Acquired for a research image collection, with no referral diagnosis. A male subject aged 73. The patient describes having numerous moles. A dermatoscopic image of a skin lesion — 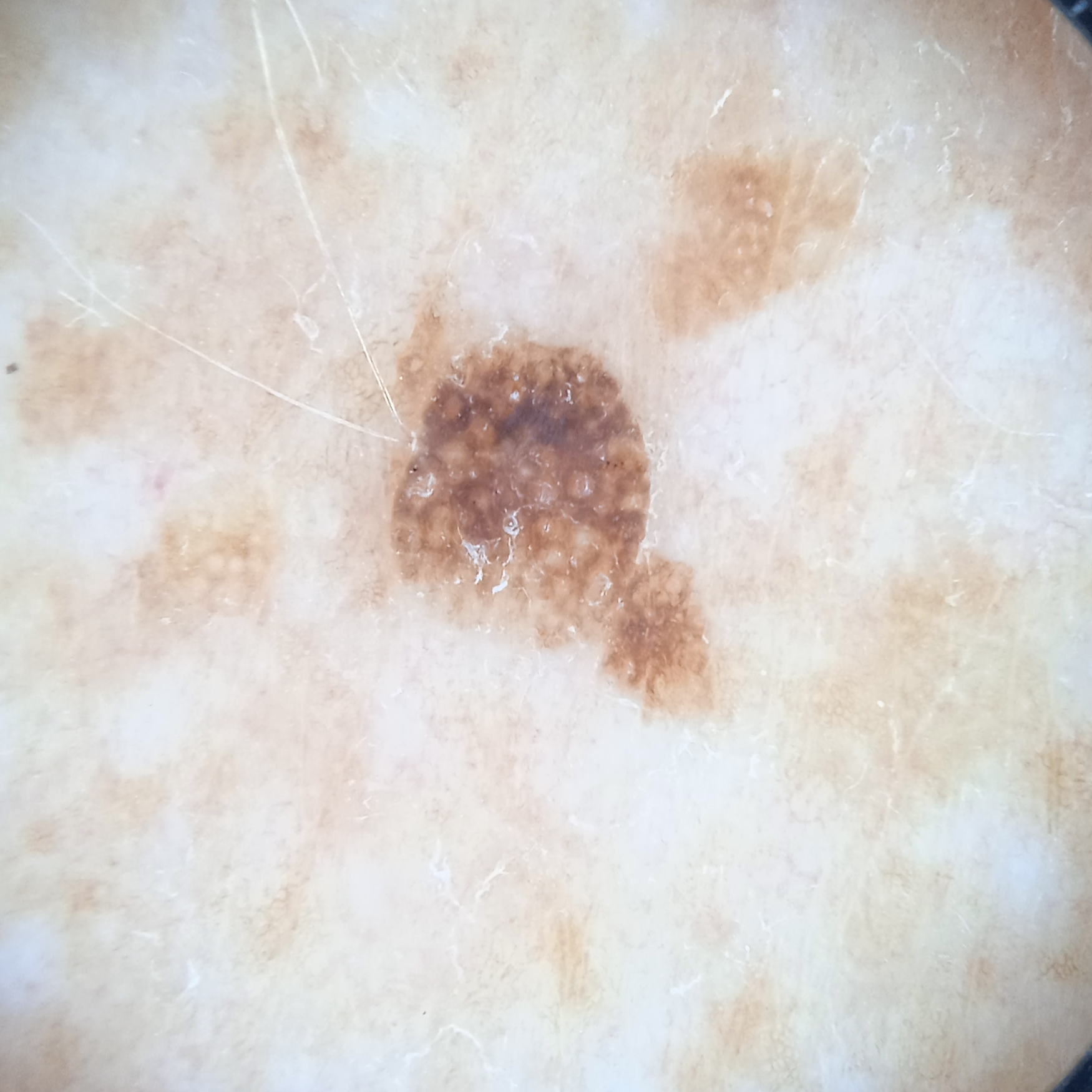Case summary: The lesion is on the back. The lesion measures approximately 5.5 mm. Impression: The consensus diagnosis for this lesion was a seborrheic keratosis.